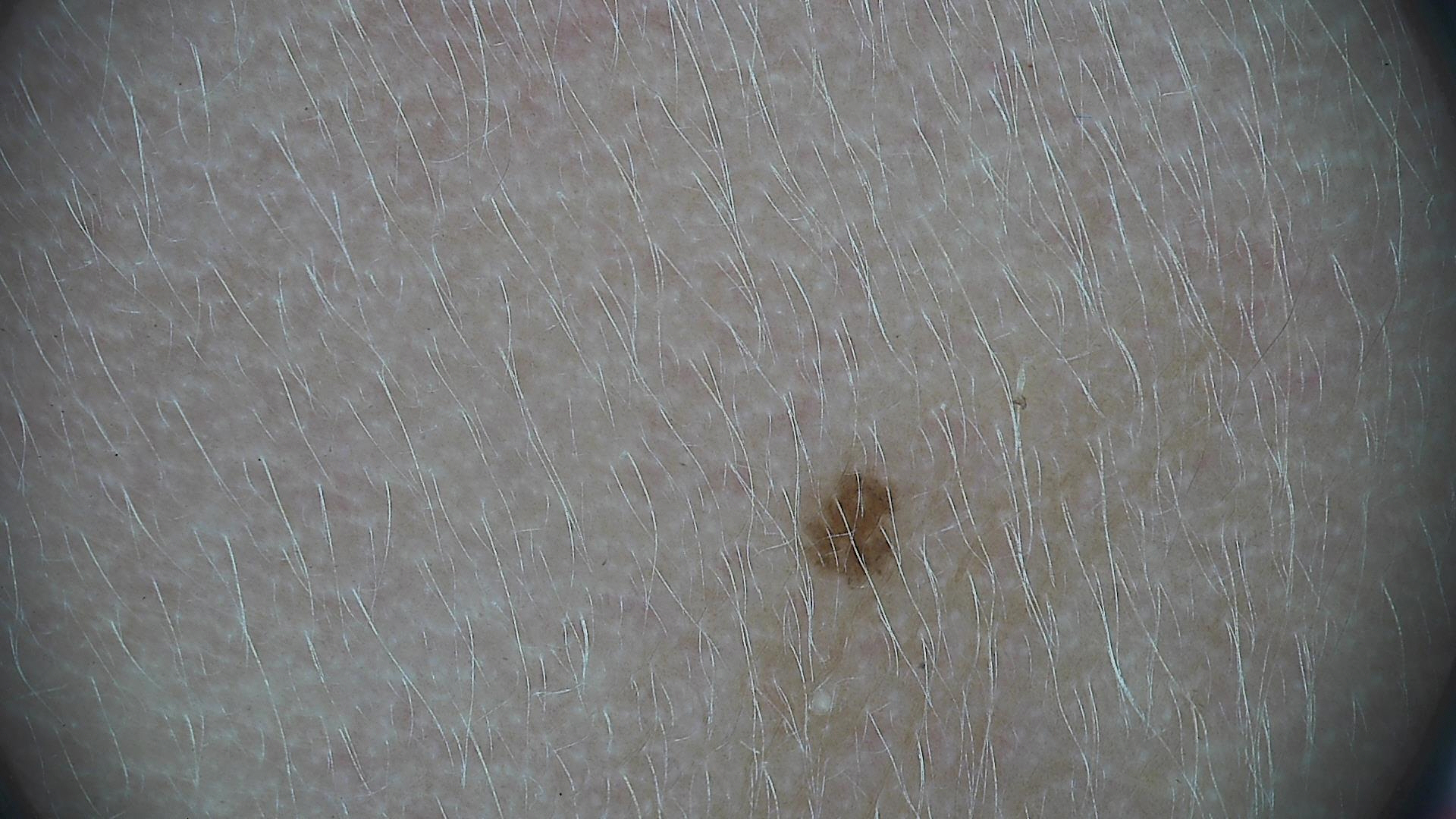label: junctional nevus (expert consensus).